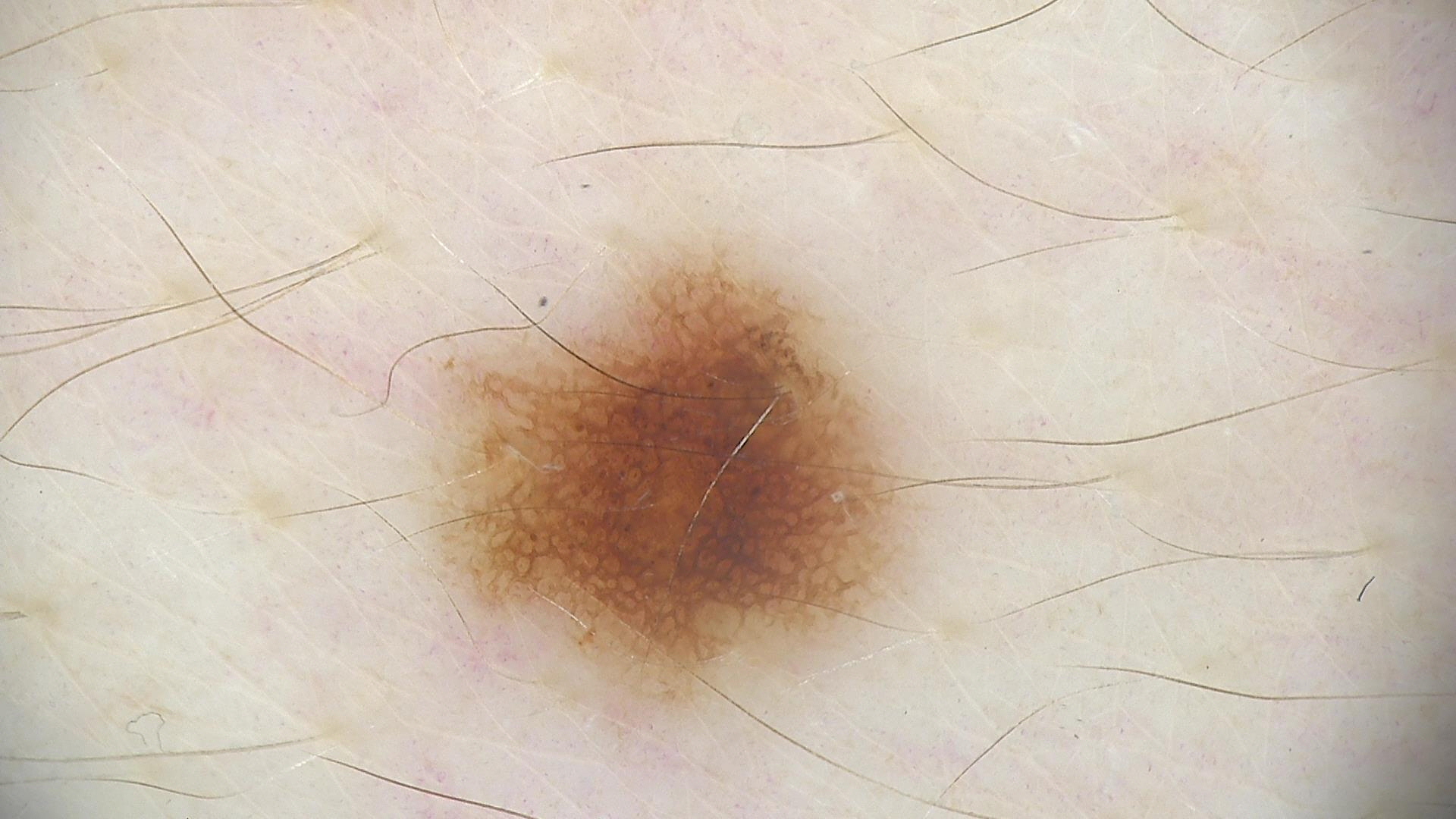A dermatoscopic image of a skin lesion. Diagnosed as a dysplastic junctional nevus.